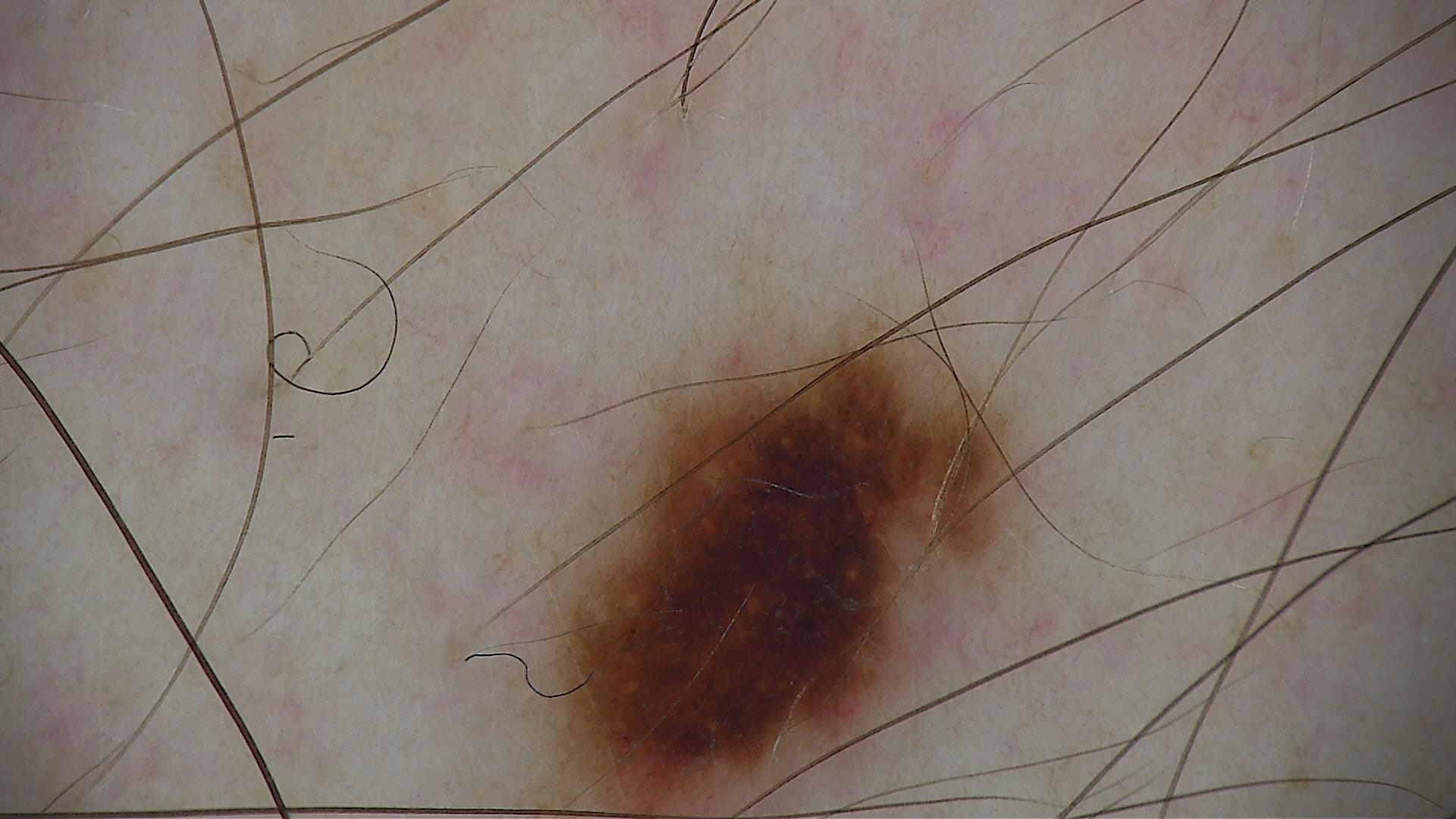The diagnosis was a dysplastic junctional nevus.